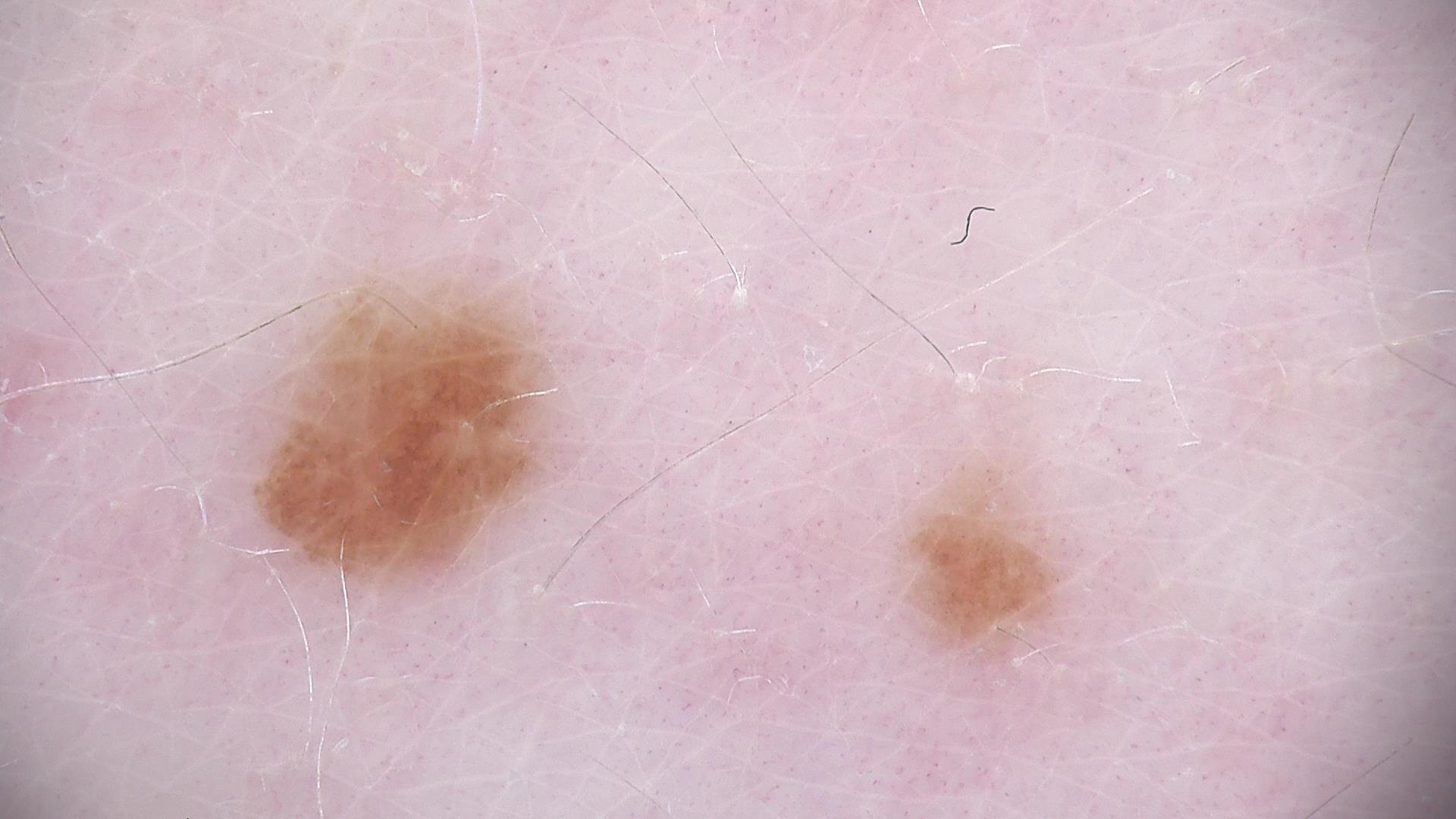diagnosis:
  name: dysplastic junctional nevus
  code: jd
  malignancy: benign
  super_class: melanocytic
  confirmation: expert consensus